A dermoscopy image of a single skin lesion.
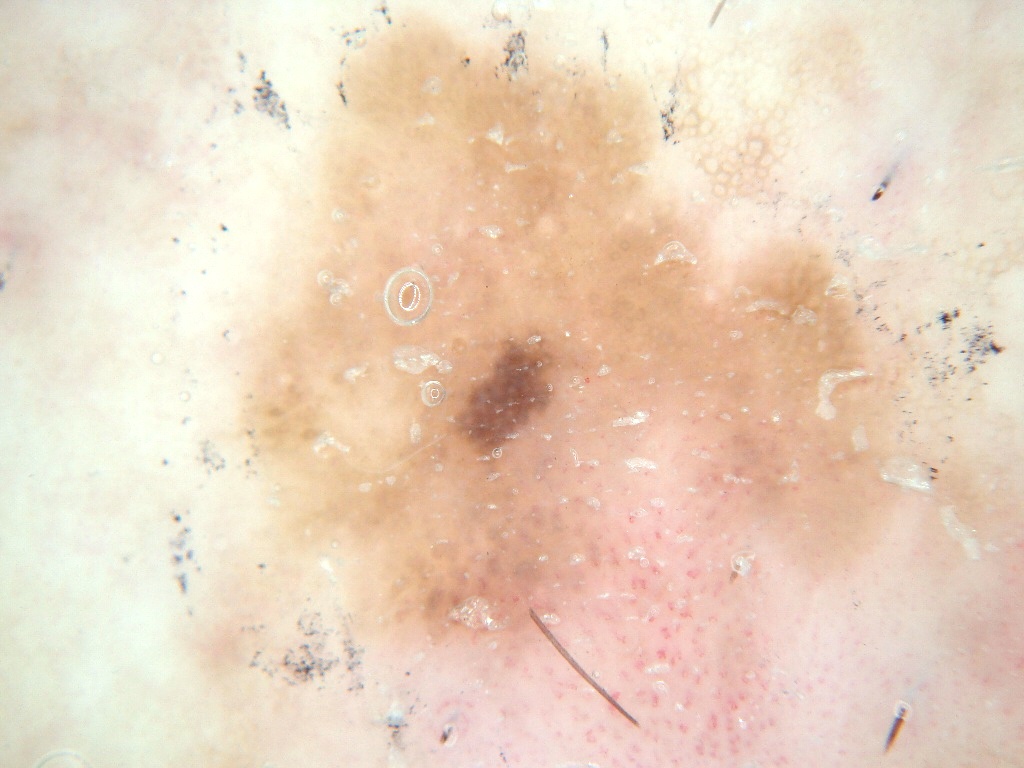The lesion occupies roughly 60% of the field.
Lesion location: 186 9 1022 766.
The clinical diagnosis was a benign lesion.